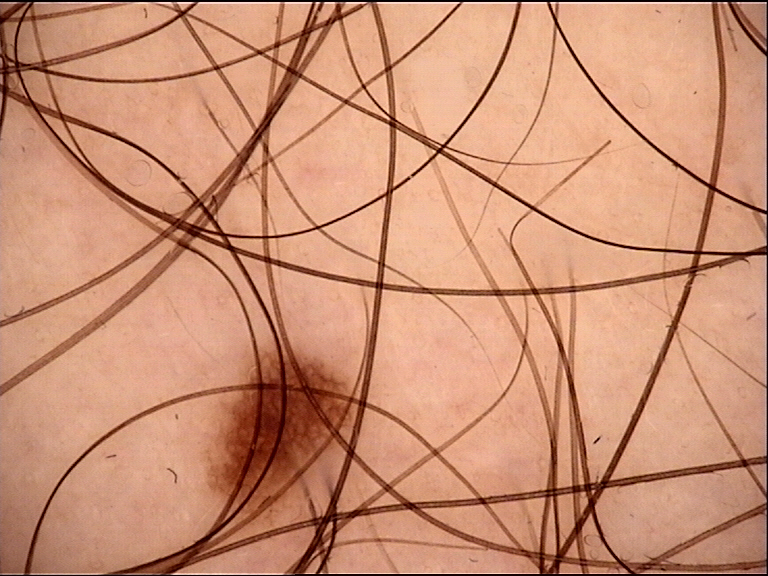A dermoscopy image of a single skin lesion. The diagnostic label was a benign lesion — a dysplastic junctional nevus.